Present for less than one week. The lesion is associated with burning, pain and bothersome appearance. The contributor reports the lesion is rough or flaky. The patient considered this skin that appeared healthy to them. Female patient, age 18–29. The leg is involved. Close-up view: 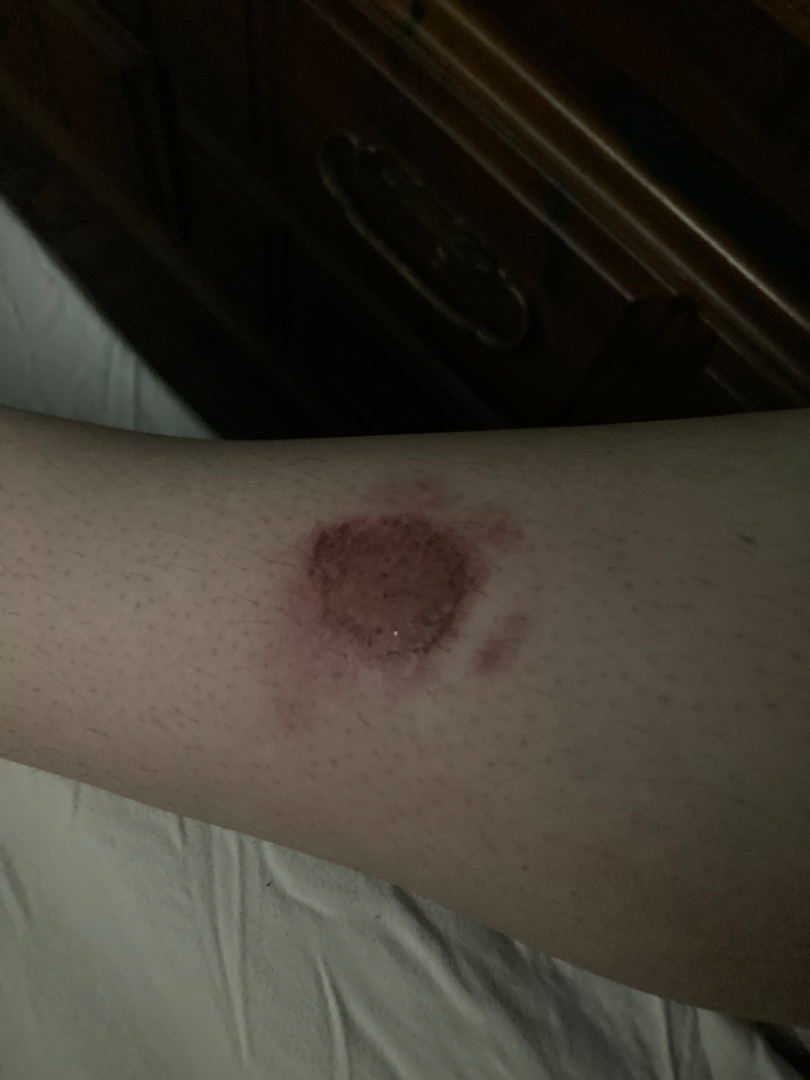Findings:
- assessment: ungradable on photographic review